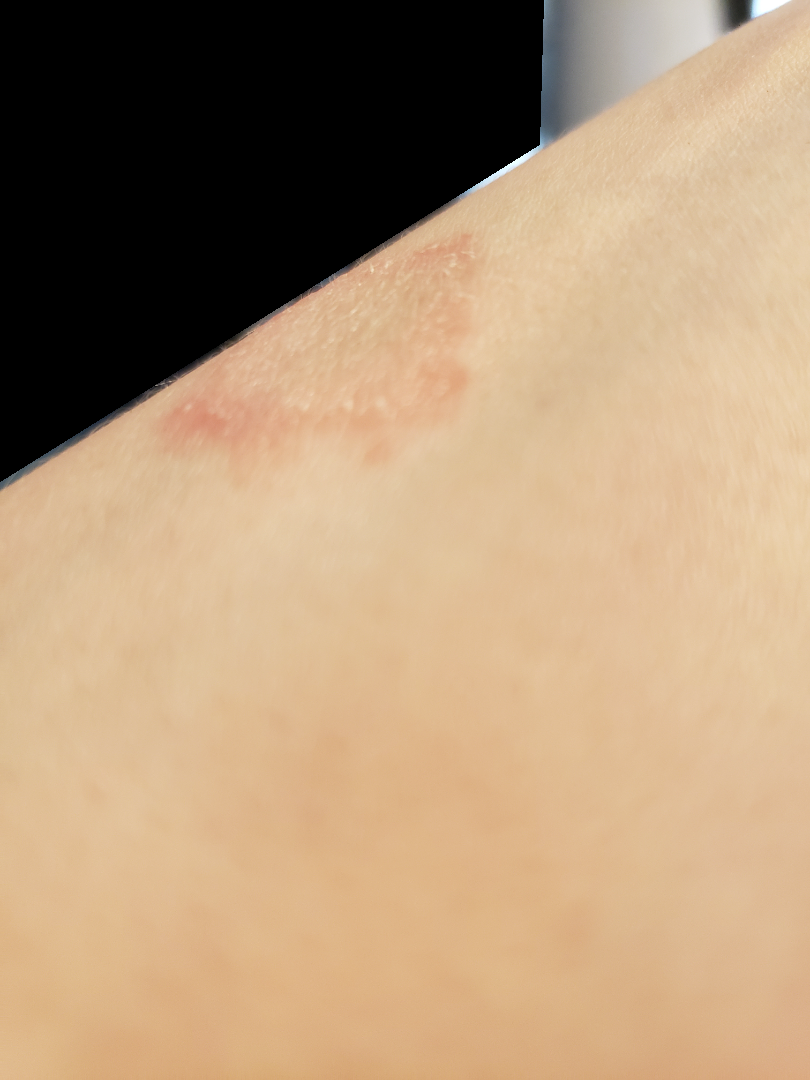skin tone=Fitzpatrick III | reported symptoms=enlargement and bothersome appearance | subject=male, age 18–29 | surface texture=rough or flaky | patient's own categorization=a rash | site=arm | symptom duration=one to four weeks | shot type=at an angle | clinical impression=the differential is split between Eczema and Tinea.